Dermoscopy of a skin lesion:
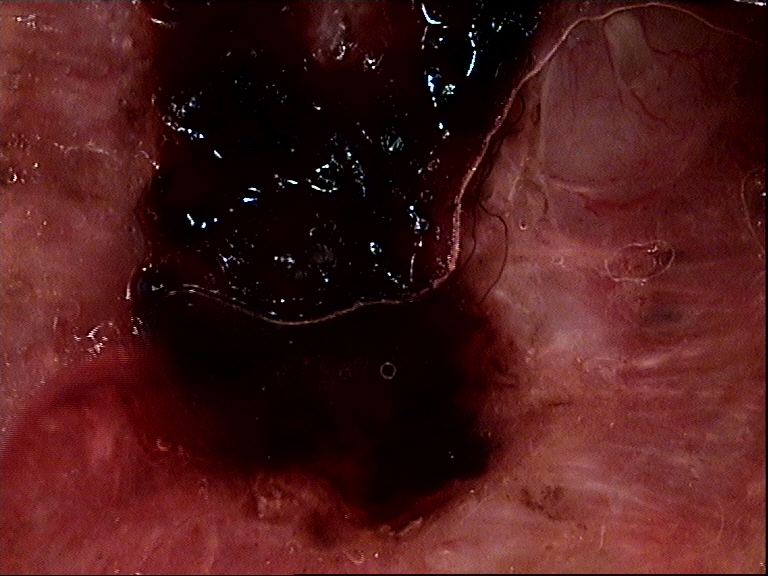Biopsy-confirmed as a malignant, keratinocytic lesion — a basal cell carcinoma.